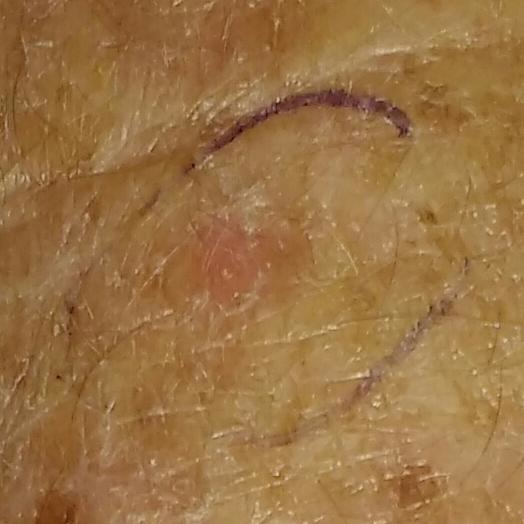patient: in their 60s
reported symptoms: itching / no bleeding
assessment: actinic keratosis (clinical consensus)